Collected as part of a research study, without a referral diagnosis; a female subject age 81: 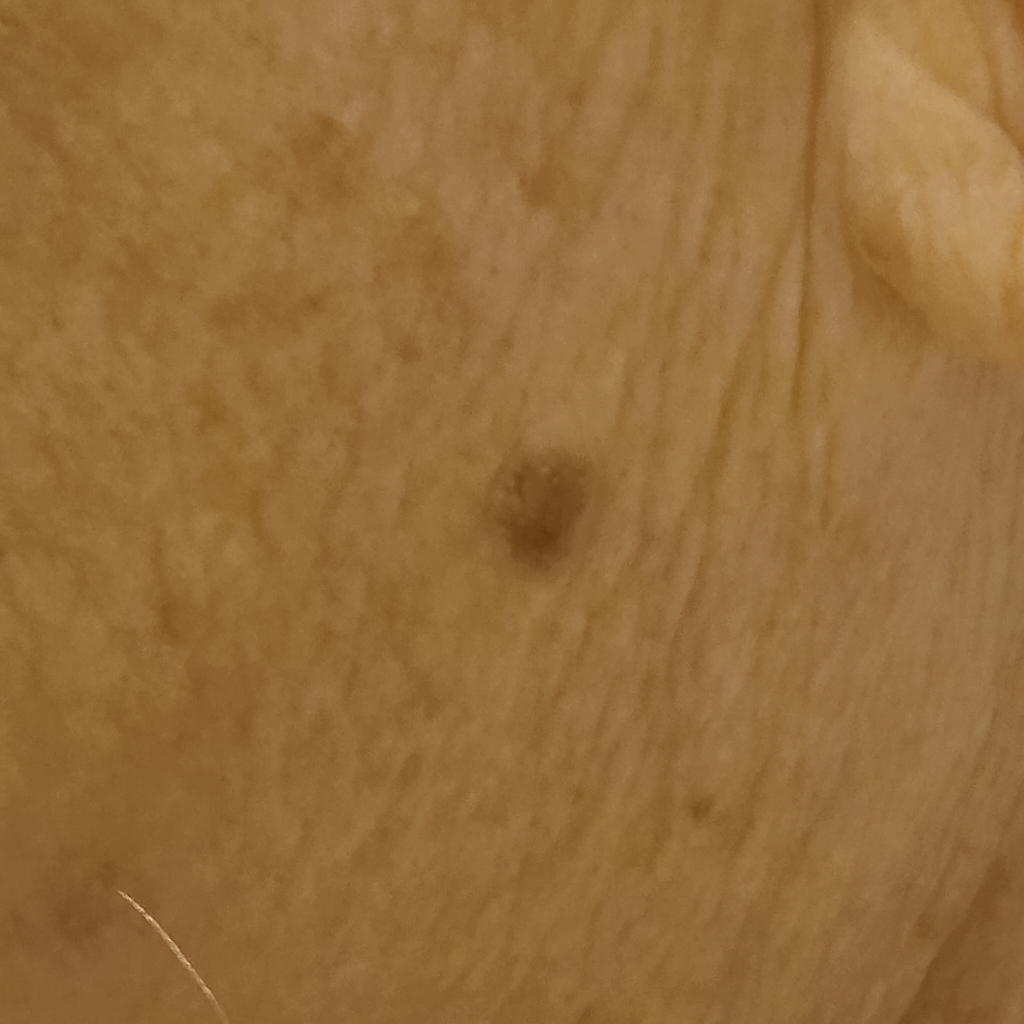Findings:
* body site: the face
* lesion size: 5.3 mm
* diagnostic label: seborrheic keratosis (dermatologist consensus)